A dermoscopic close-up of a skin lesion.
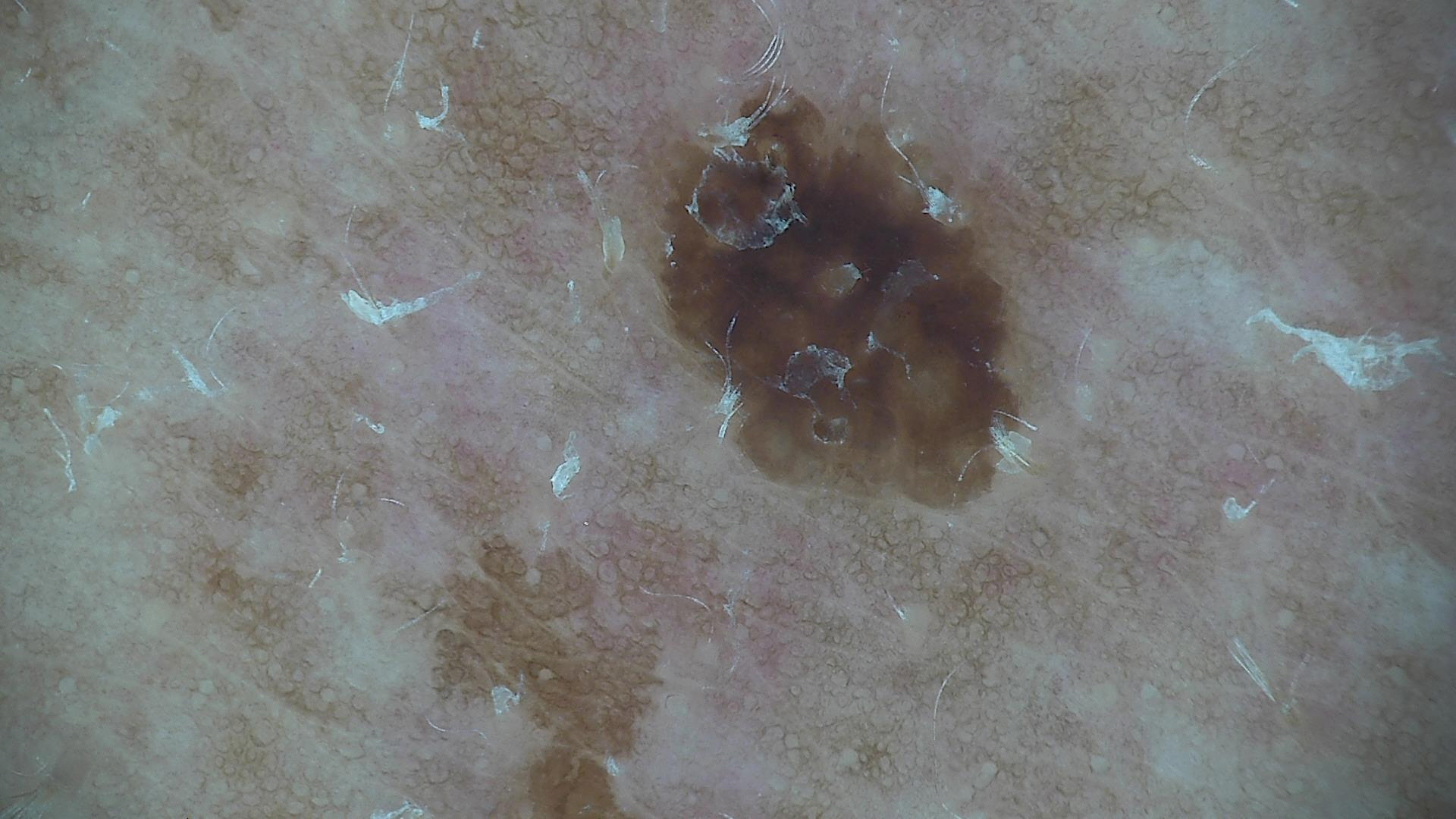The morphology is that of a keratinocytic lesion.
The diagnostic label was a benign lesion — a seborrheic keratosis.